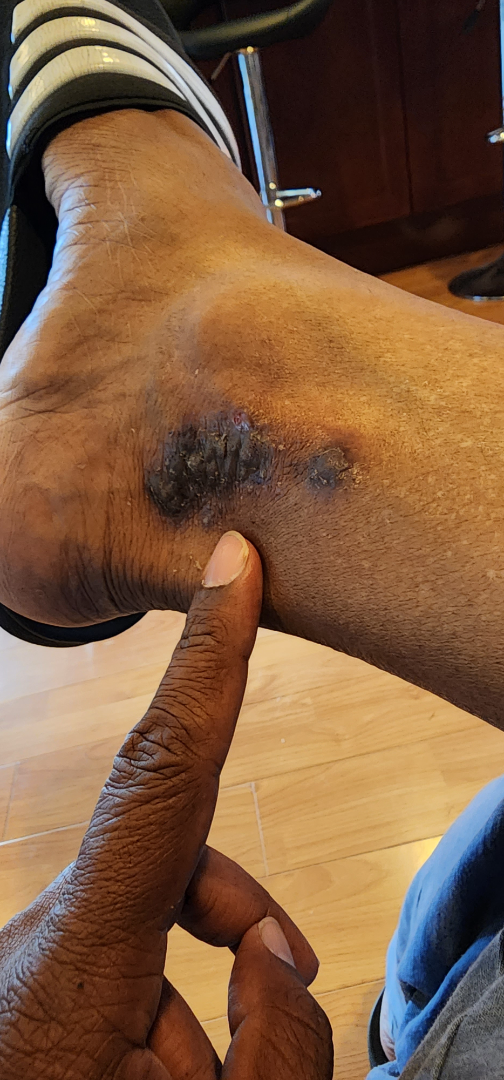Assessment: On independent review by the dermatologists: the favored diagnosis is Kaposi's sarcoma of skin; a more distant consideration is Psoriasis; lower on the differential is Lichen Simplex Chronicus; less likely is Lichen planus/lichenoid eruption; less probable is Hemangioma; a remote consideration is Melanoma.